A dermoscopic image of a skin lesion.
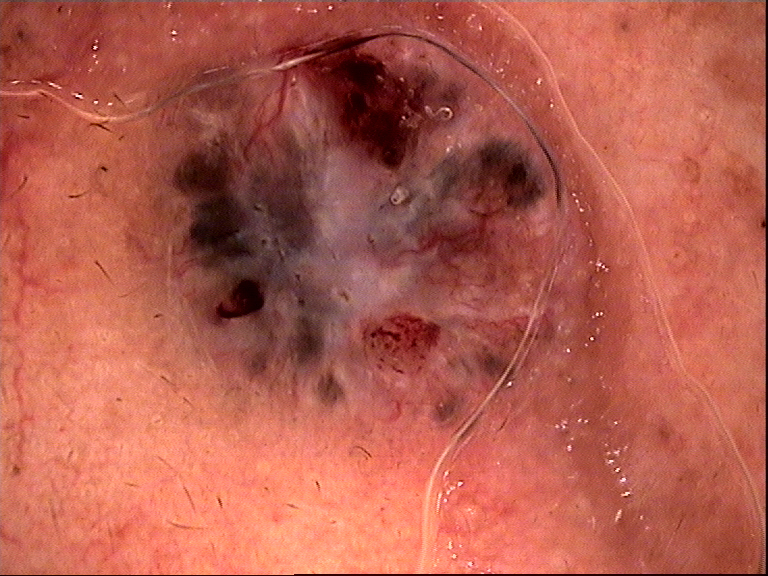Histopathology confirmed a keratinocytic lesion — a basal cell carcinoma.